A dermoscopic image of a skin lesion.
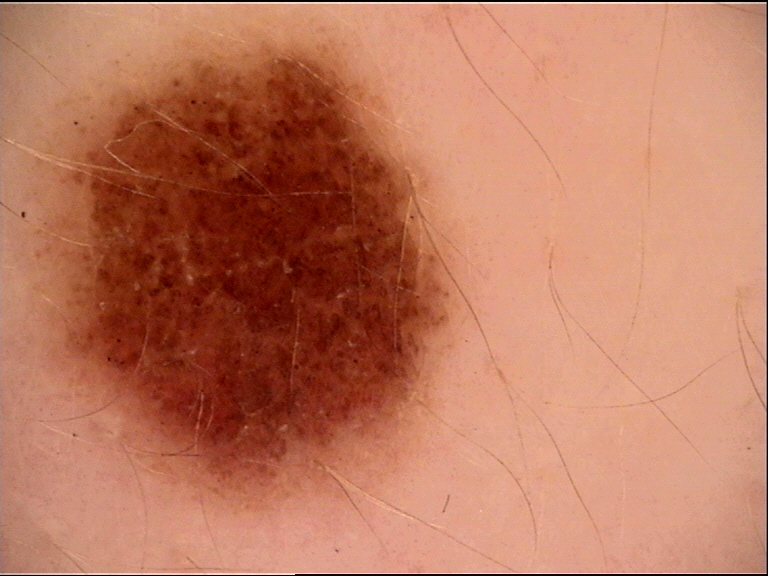assessment = dysplastic compound nevus (expert consensus).